A dermatoscopic image of a skin lesion: 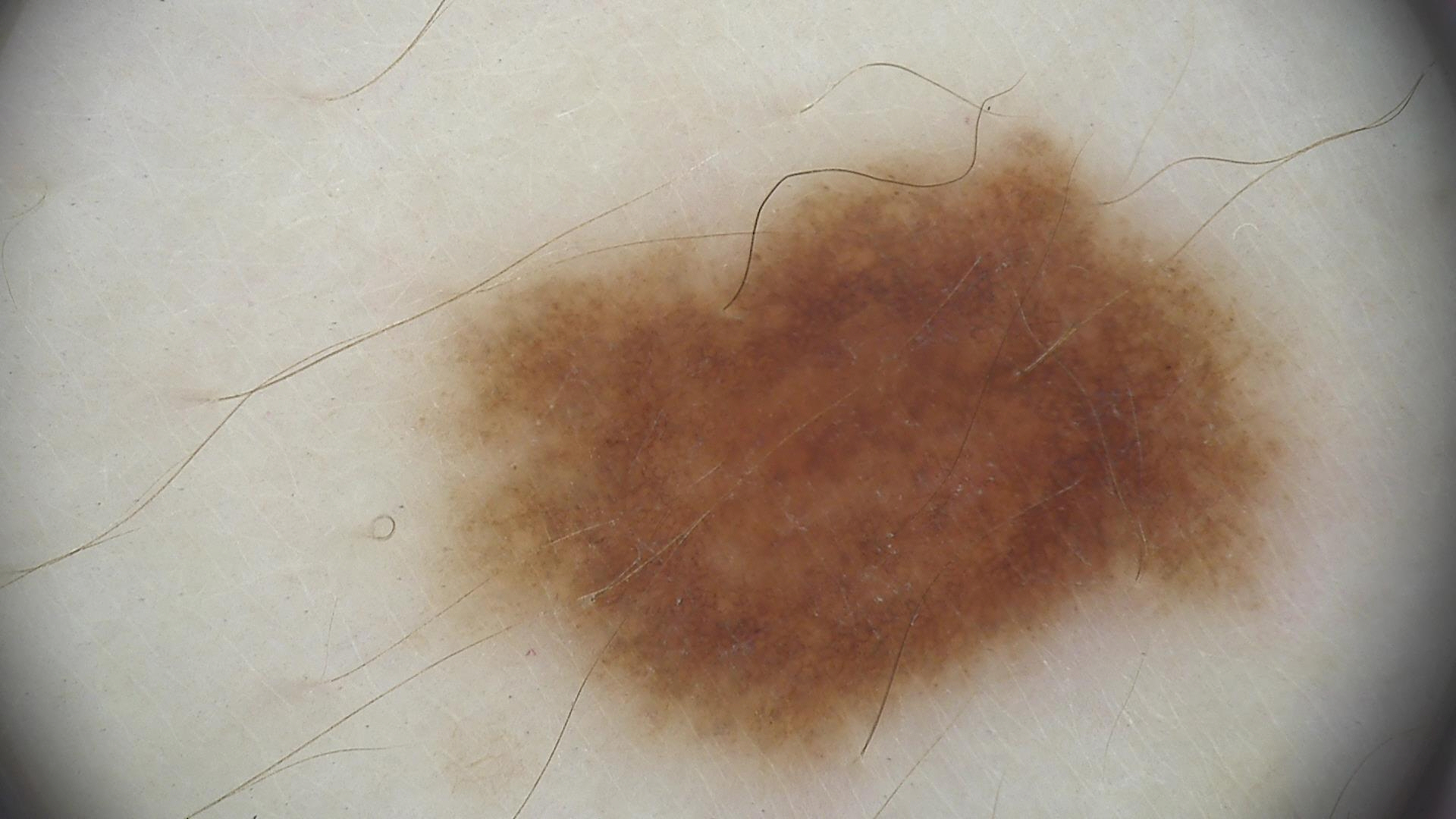class=dysplastic junctional nevus (expert consensus).